The patient is a male about 50 years old · a dermoscopy image of a single skin lesion:
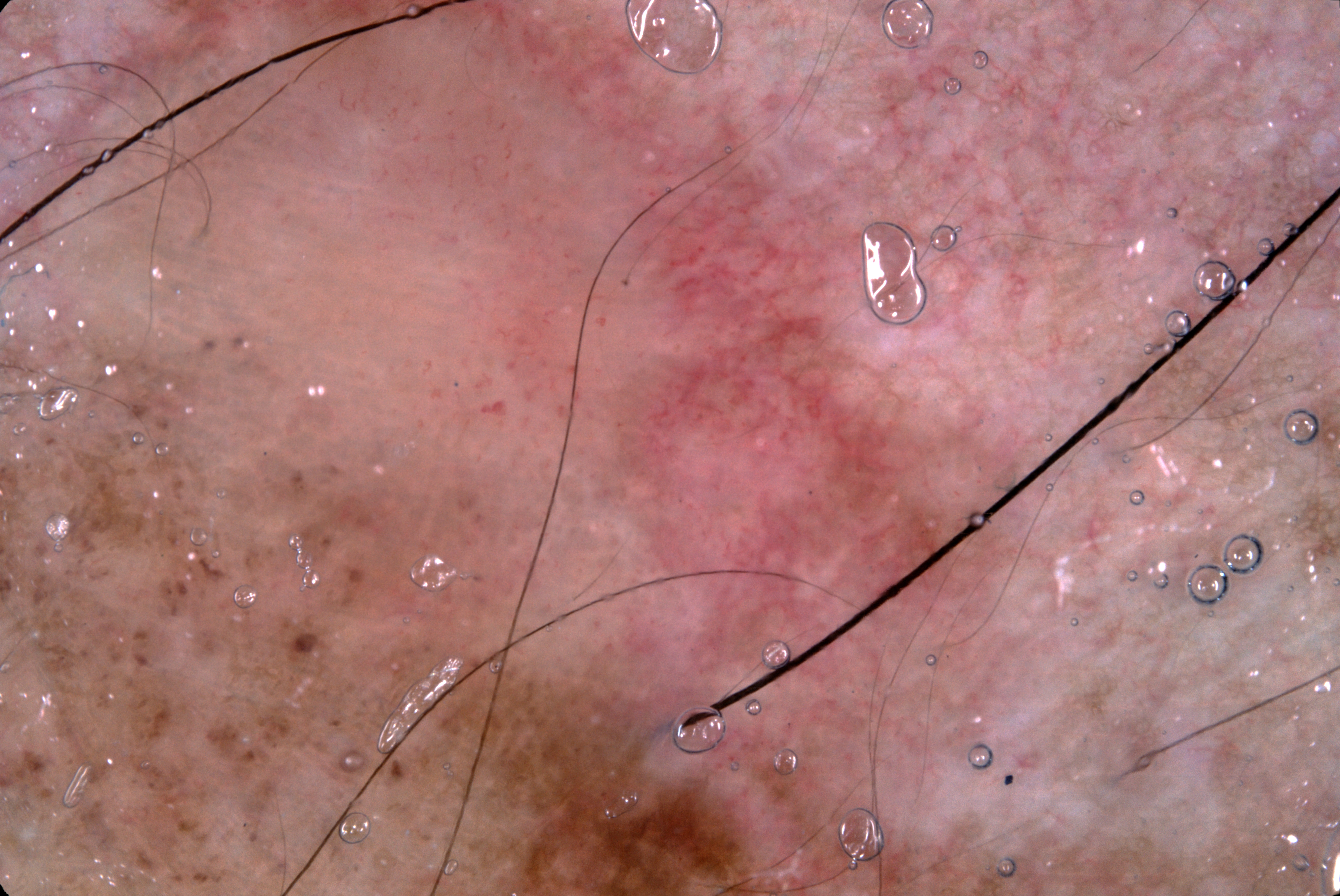Case summary: As (left, top, right, bottom), the lesion spans 11/6/1082/895. Dermoscopy demonstrates negative network, with no milia-like cysts, pigment network, or streaks. A prominent lesion filling much of the field. Diagnosis: Confirmed on histopathology as a melanoma.